A smartphone photograph of a skin lesion; a subject in their 60s — 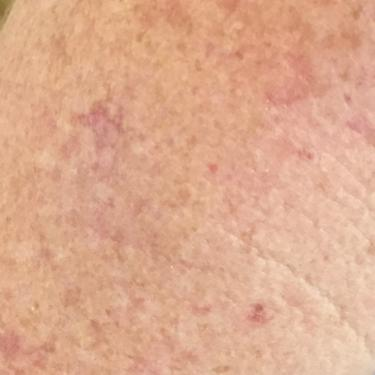Findings:
The lesion is on an arm. Per patient report, the lesion itches.
Conclusion:
Expert review favored an actinic keratosis.